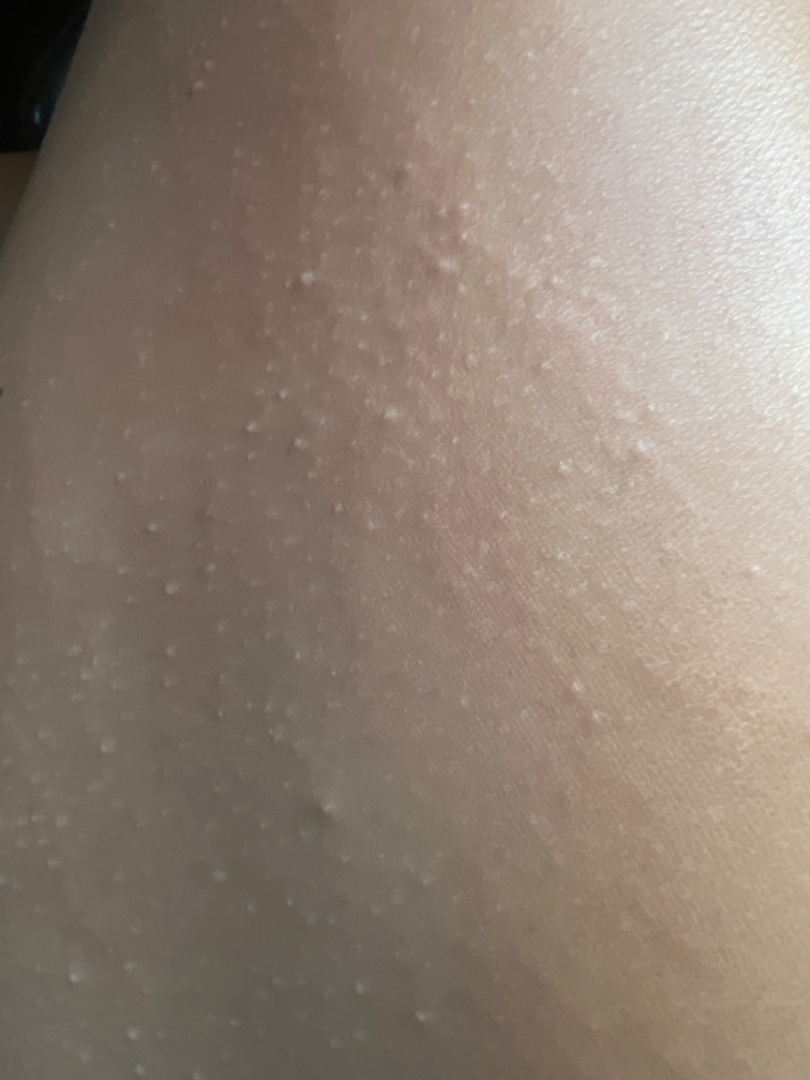The lesion involves the leg.
The patient notes itching.
The patient reported no systemic symptoms.
A close-up photograph.
Reported duration is one to three months.
Single-reviewer assessment: the favored diagnosis is Keratosis pilaris; with consideration of Lichen nitidus; also raised was Lichen spinulosus.